Female contributor, age 40–49. This is a close-up image. Located on the leg: 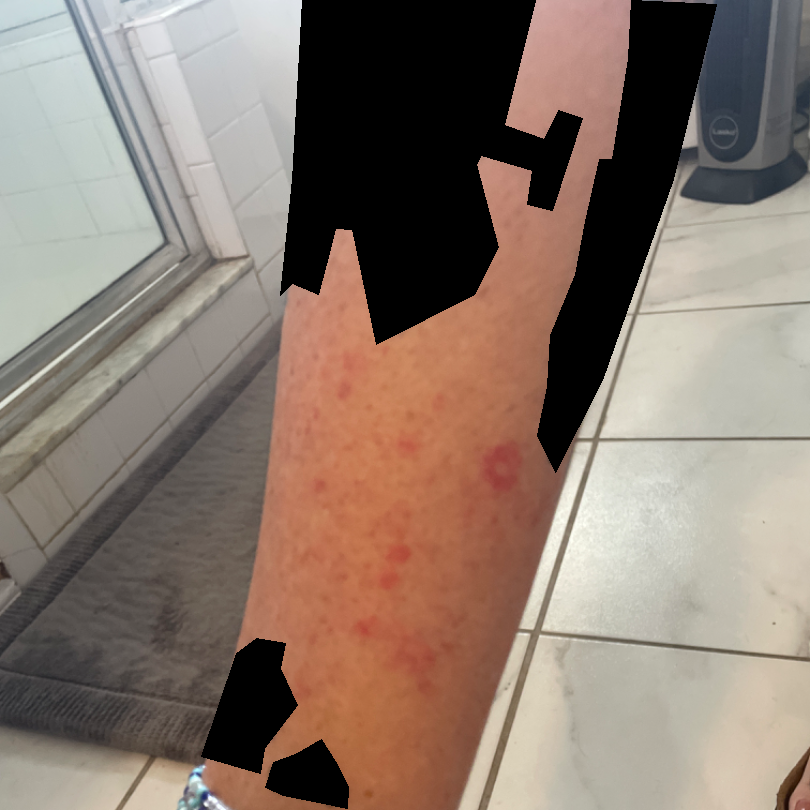Patient information: The patient reports the lesion is flat. Review: Allergic Contact Dermatitis (0.55); Insect Bite (0.27); Eczema (0.18).